Dermoscopy of a skin lesion.
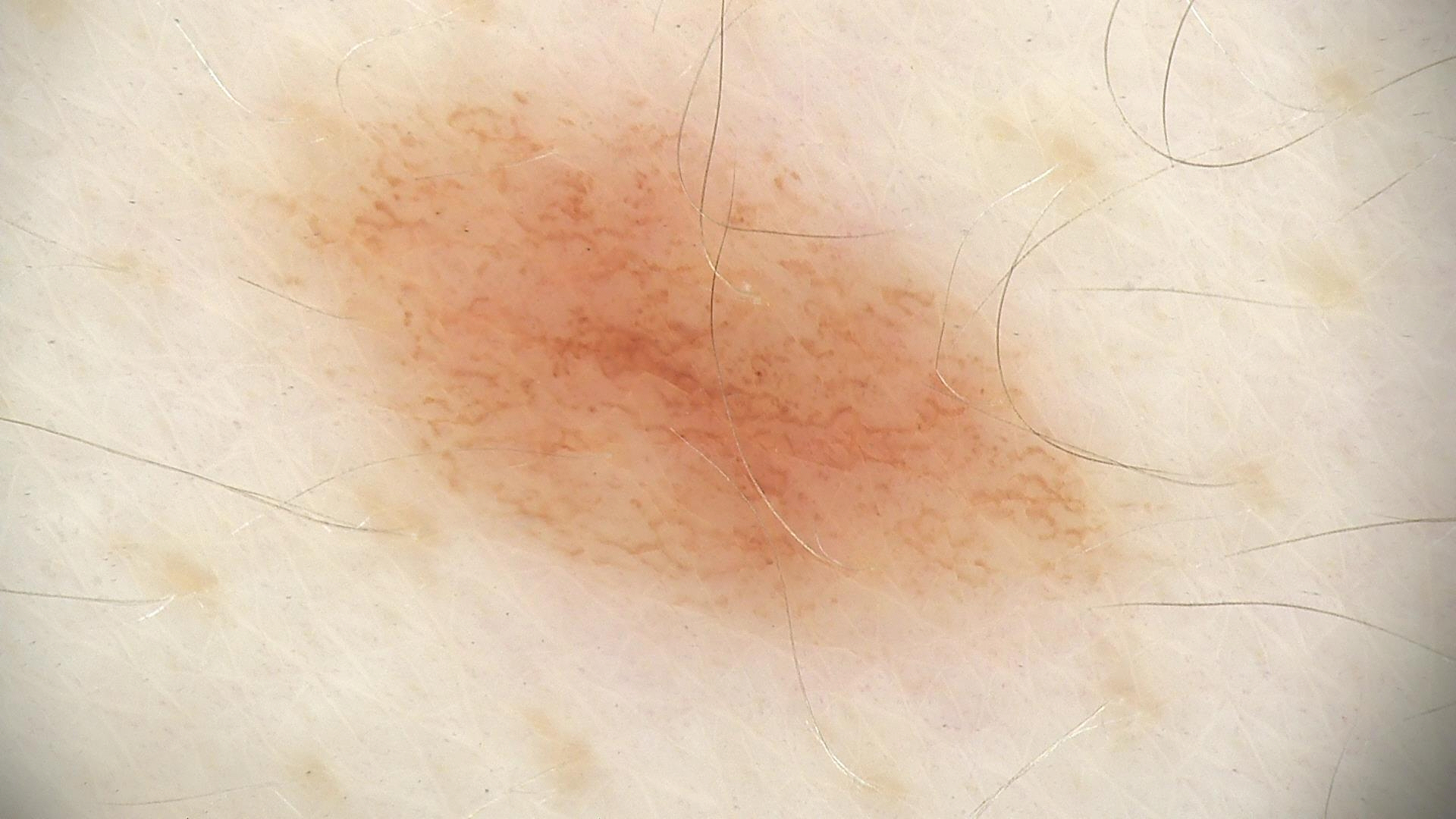Case:
– diagnostic label: dysplastic junctional nevus (expert consensus)